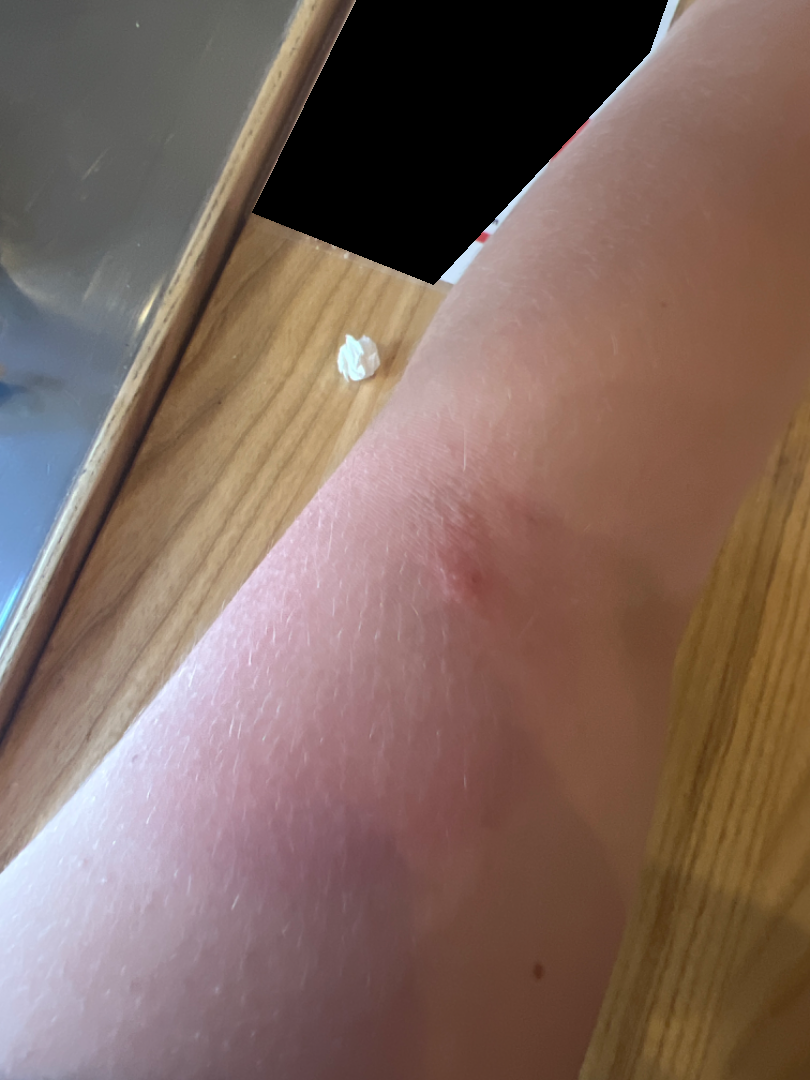assessment = not assessable; photo taken = close-up; subject = female, age 18–29; anatomic site = arm.